Per the chart, a previous melanoma; a male patient about 80 years old; a skin lesion imaged with contact-polarized dermoscopy.
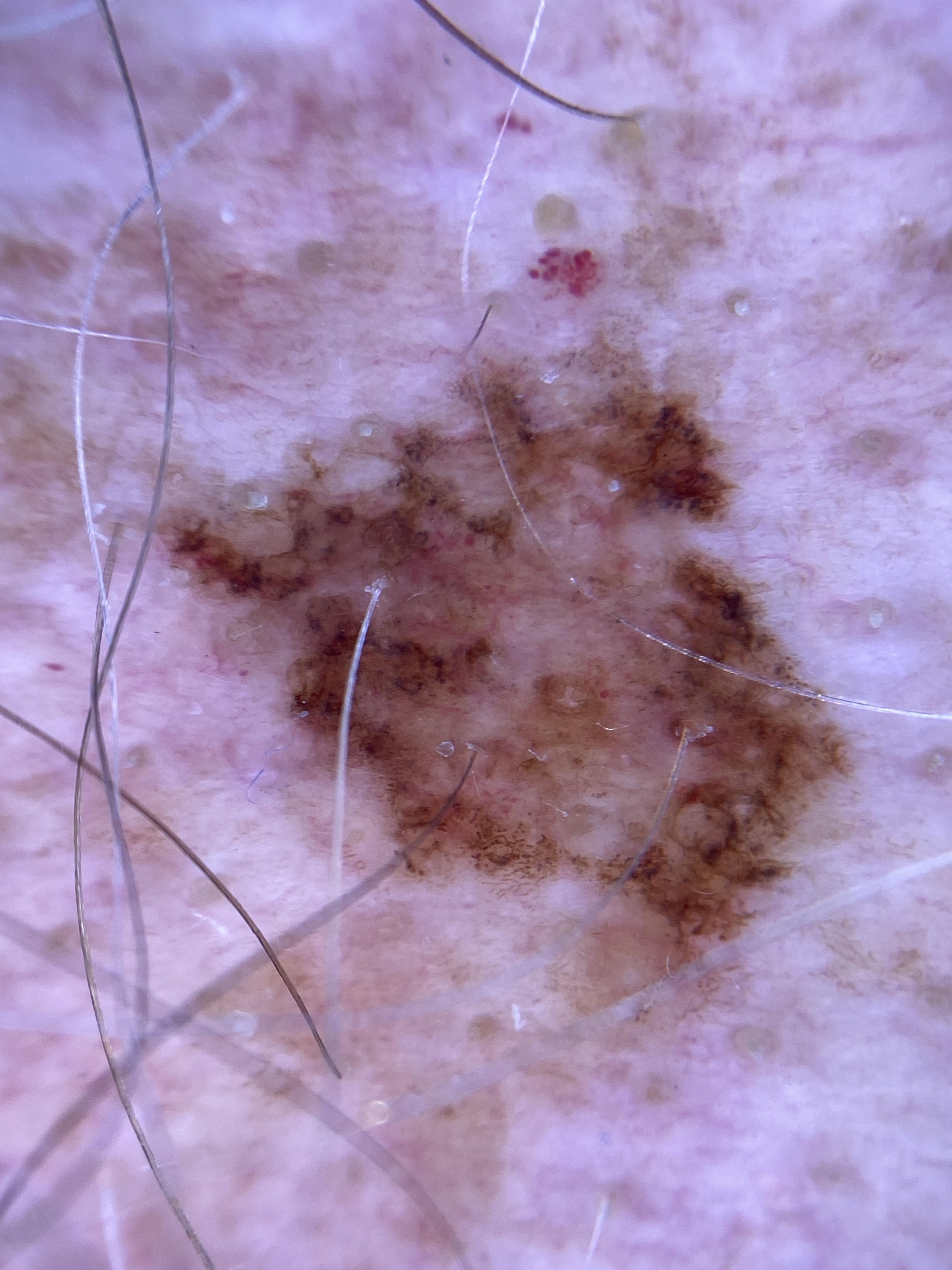diagnosis:
  name: Melanoma
  malignancy: malignant
  confirmation: histopathology